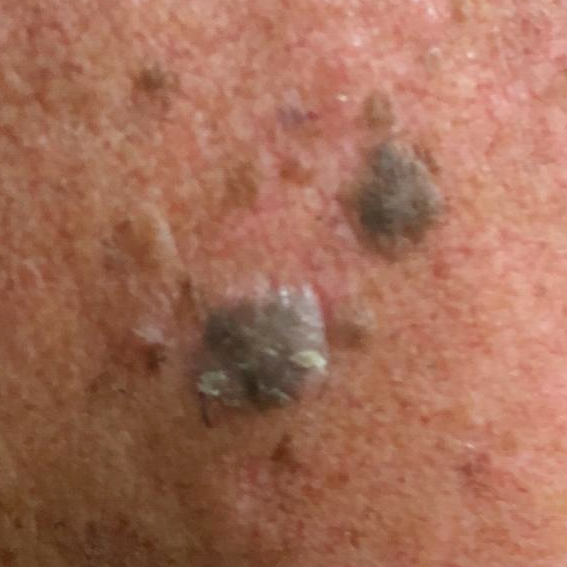– subject · male, aged 59
– image type · smartphone clinical photo
– region · the face
– symptoms · growth, elevation / no bleeding
– assessment · seborrheic keratosis (clinical consensus)